Imaged for a research study, with no referral diagnosis recorded · a dermoscopy image of a skin lesion · a female subject age 81:
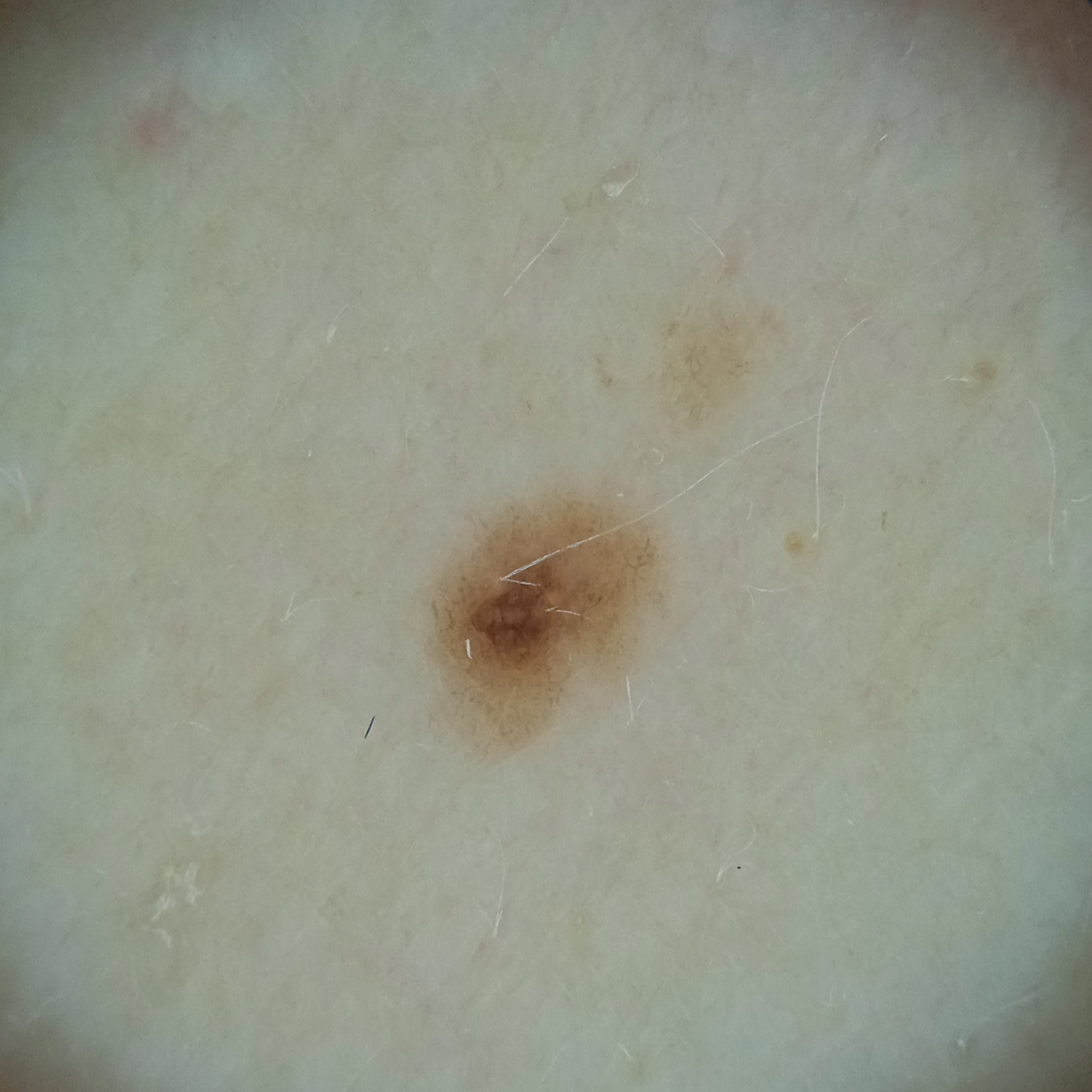site=the back; lesion size=2.7 mm; diagnosis=melanocytic nevus (dermatologist consensus).